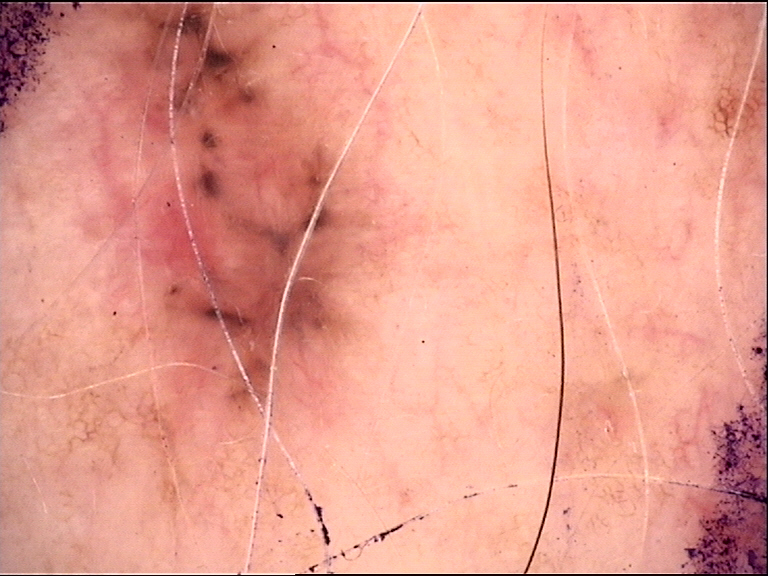Conclusion:
Histopathology confirmed a basal cell carcinoma.